An image taken at an angle, the top or side of the foot is involved: 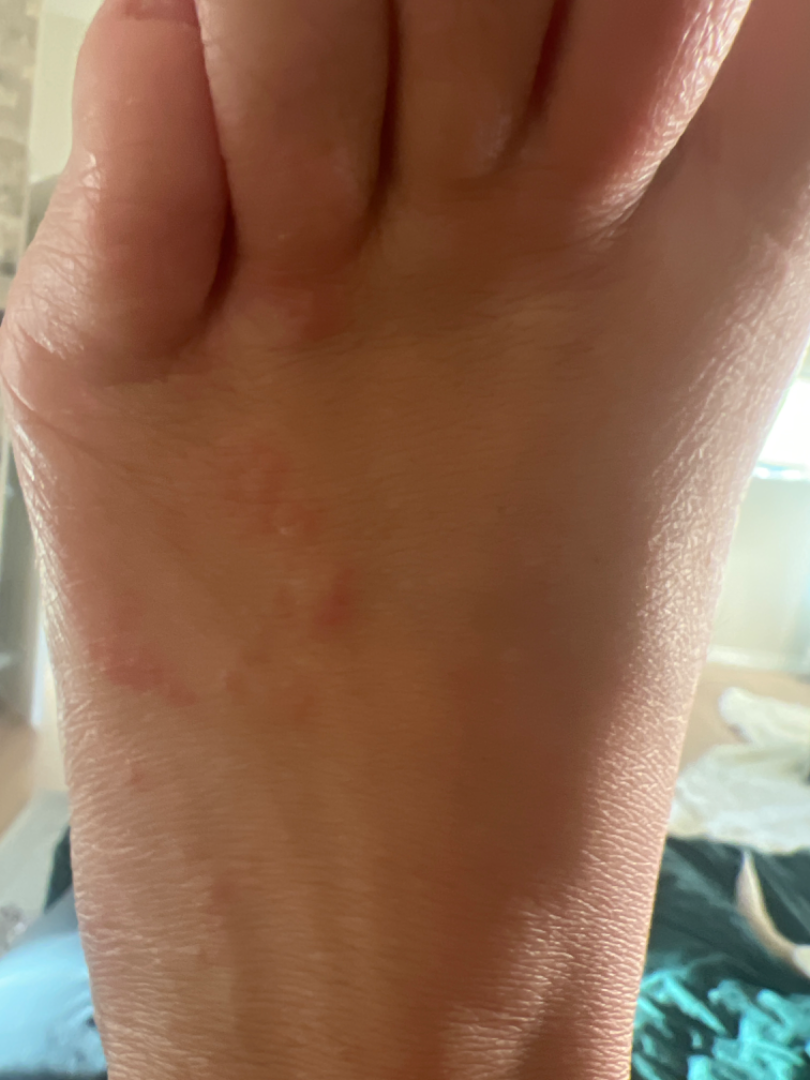Clinical context:
Texture is reported as raised or bumpy.
Assessment:
On photographic review by a dermatologist: the differential is split between Tinea and Cutaneous larva migrans; less probable is Eczema.